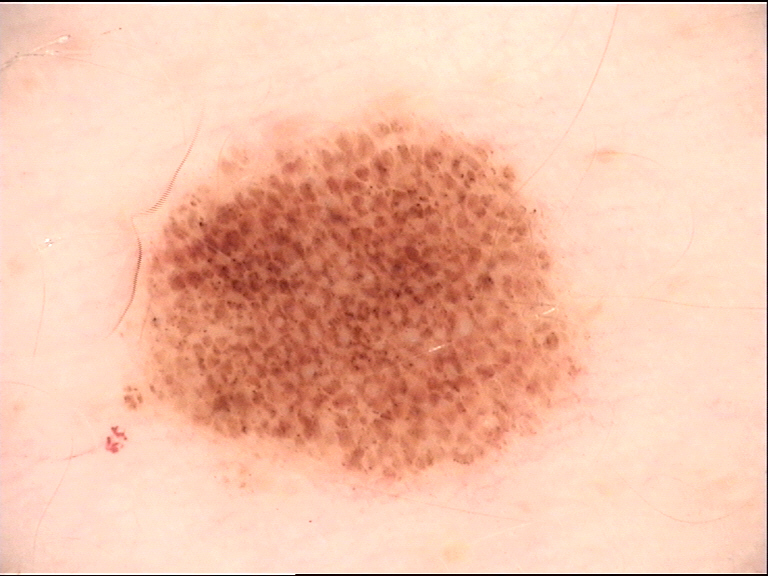class: junctional nevus (expert consensus).